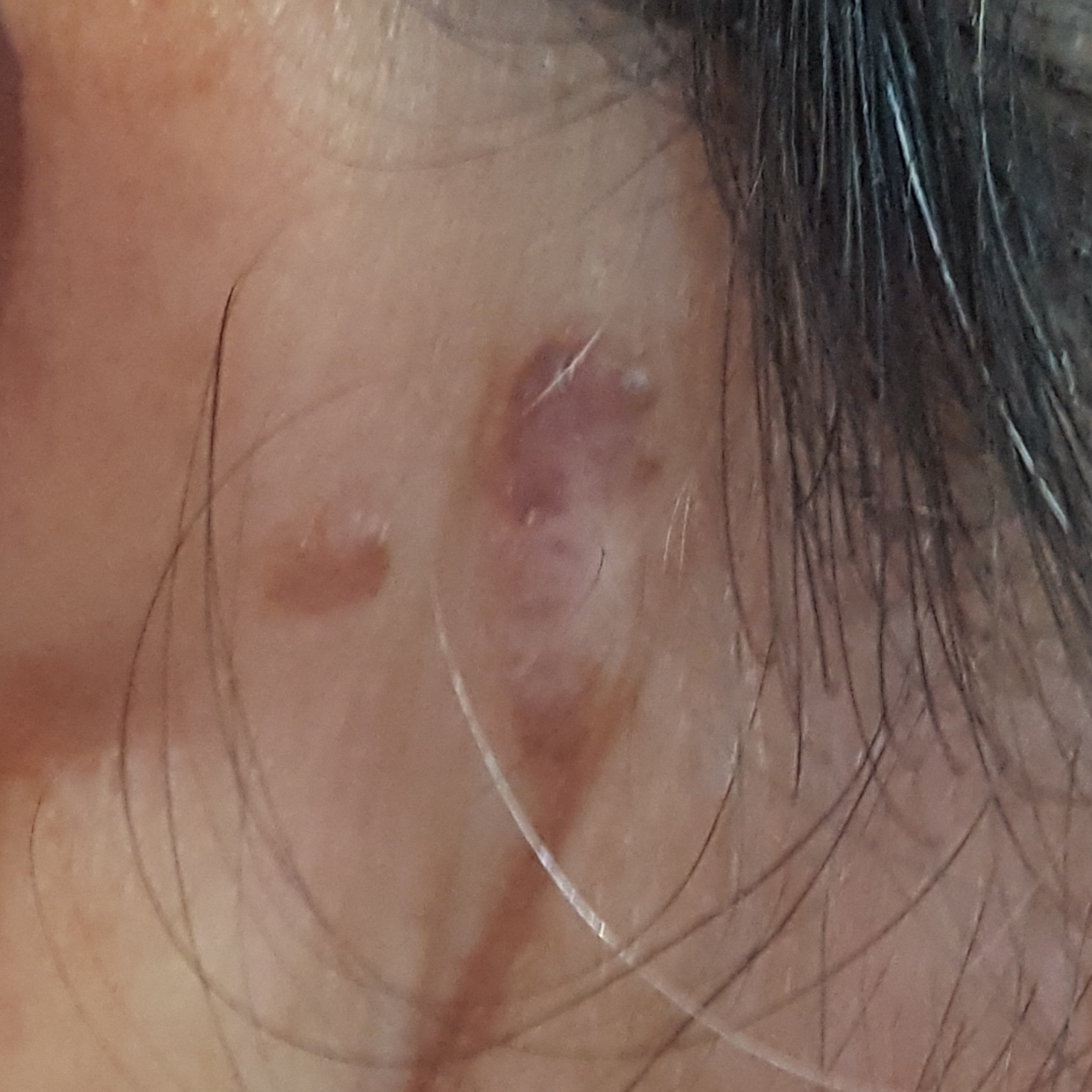A clinical photo of a skin lesion taken with a smartphone. Per patient report, the lesion is elevated, itches, and has grown, but has not bled and does not hurt. The consensus clinical diagnosis was a seborrheic keratosis.